FST II. A skin lesion imaged with a dermatoscope.
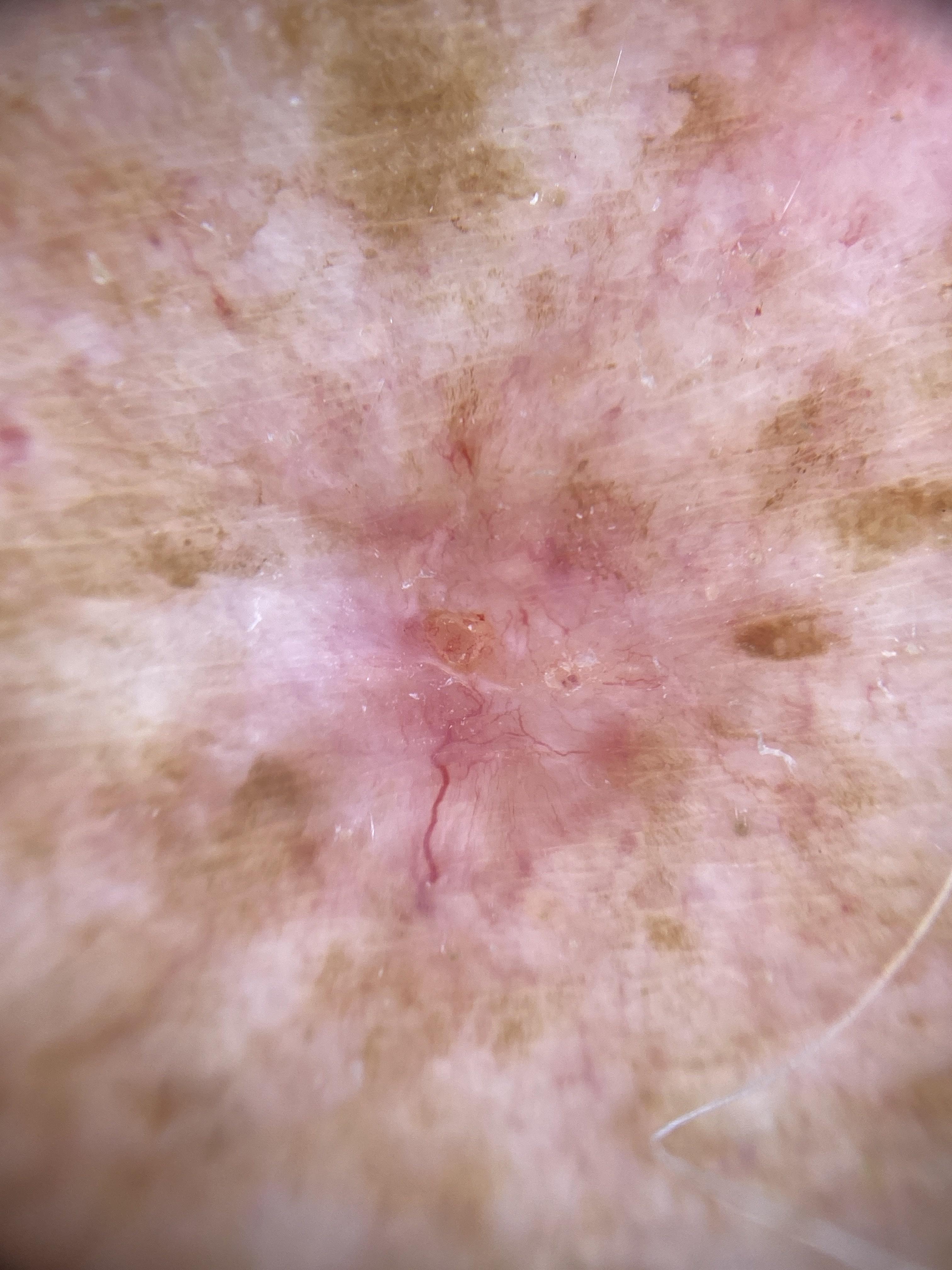Case summary: Located on the trunk, specifically the anterior trunk. Diagnosis: Histopathology confirmed a basal cell carcinoma.